A skin lesion imaged with a dermatoscope: 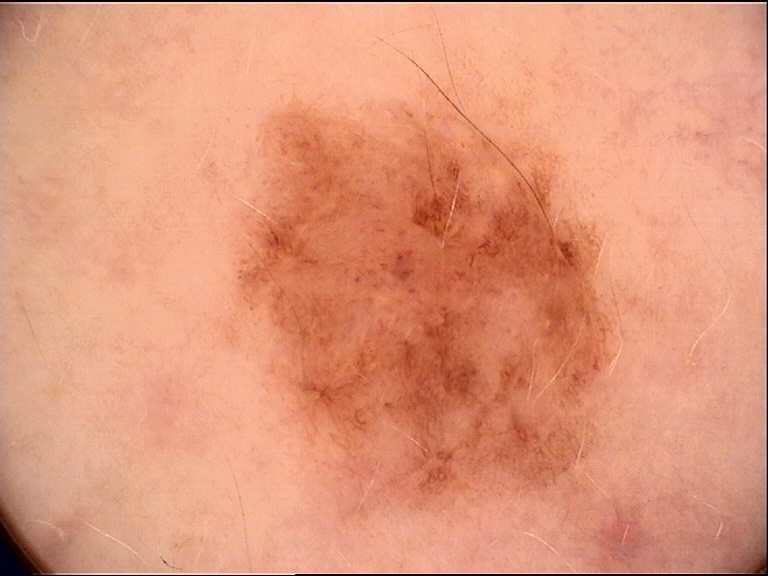<case>
  <diagnosis>
    <name>compound nevus</name>
    <code>cb</code>
    <malignancy>benign</malignancy>
    <super_class>melanocytic</super_class>
    <confirmation>expert consensus</confirmation>
  </diagnosis>
</case>